Close-up view; the patient is 18–29, male; located on the front of the torso, top or side of the foot, back of the hand, leg and arm:
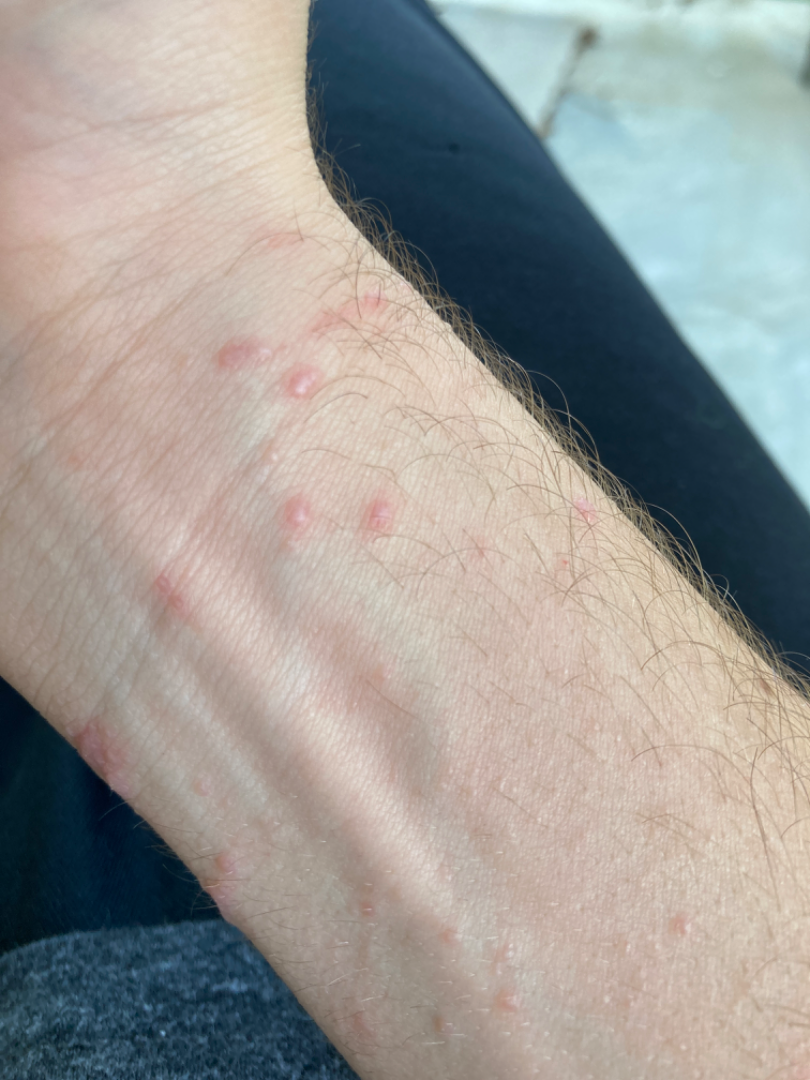On photographic review, Scabies, Insect Bite and Allergic Contact Dermatitis were each considered, in no particular order.